Reported lesion symptoms include pain and burning; the subject is 40–49, female; no relevant systemic symptoms; skin tone: Fitzpatrick skin type II; a close-up photograph; the affected area is the arm; texture is reported as raised or bumpy and fluid-filled: 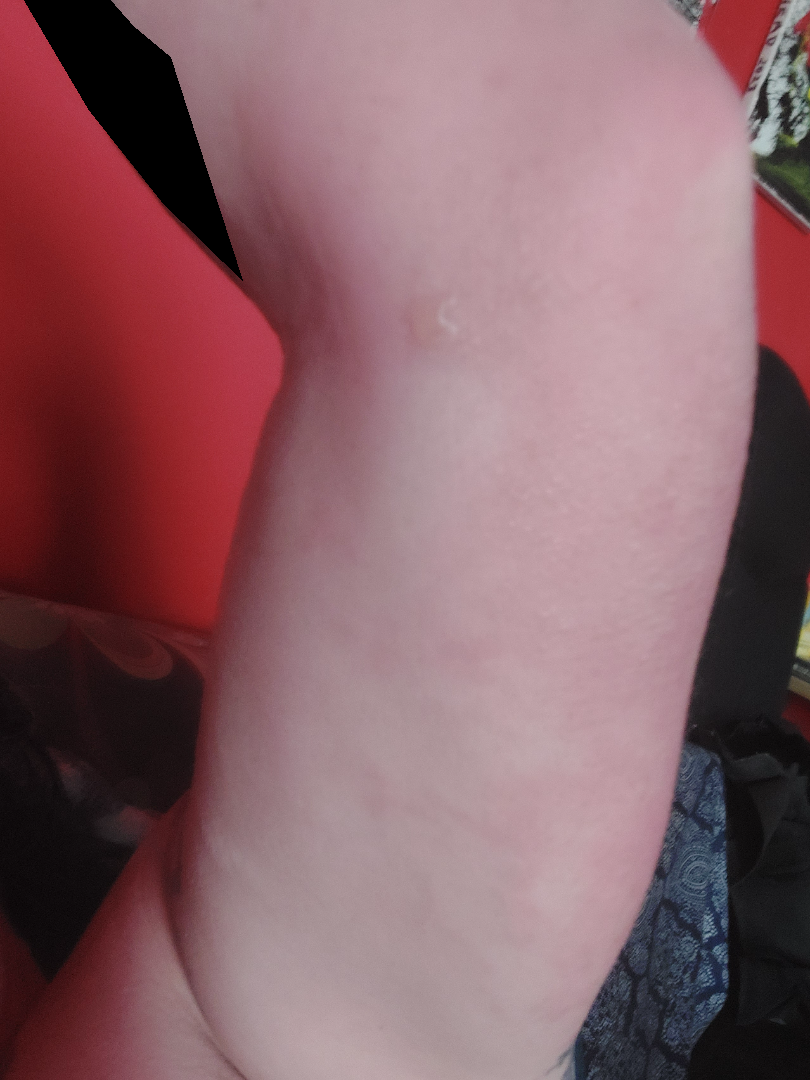{
  "assessment": "could not be assessed"
}